Skin tone: Fitzpatrick I · the contributor notes the condition has been present for more than one year · this image was taken at a distance · the lesion is described as raised or bumpy and rough or flaky: 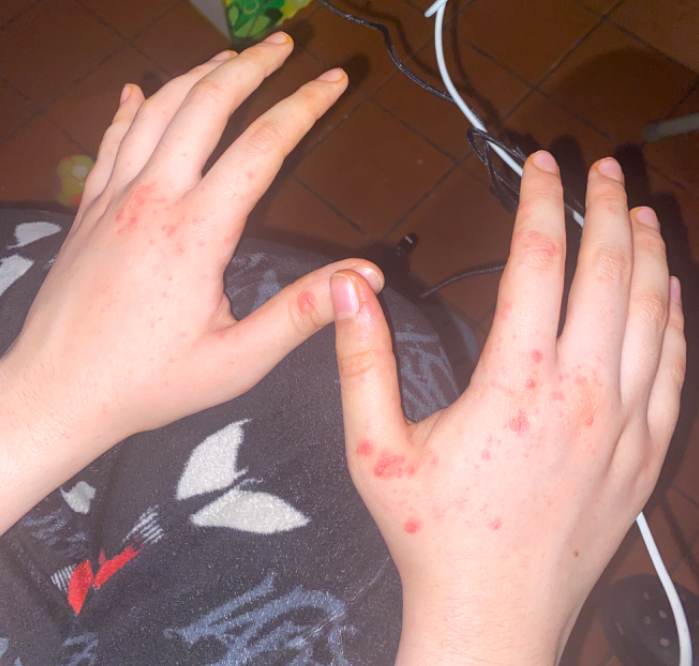On photographic review by a dermatologist, the differential, in no particular order, includes Impetigo, Molluscum Contagiosum and Allergic Contact Dermatitis.